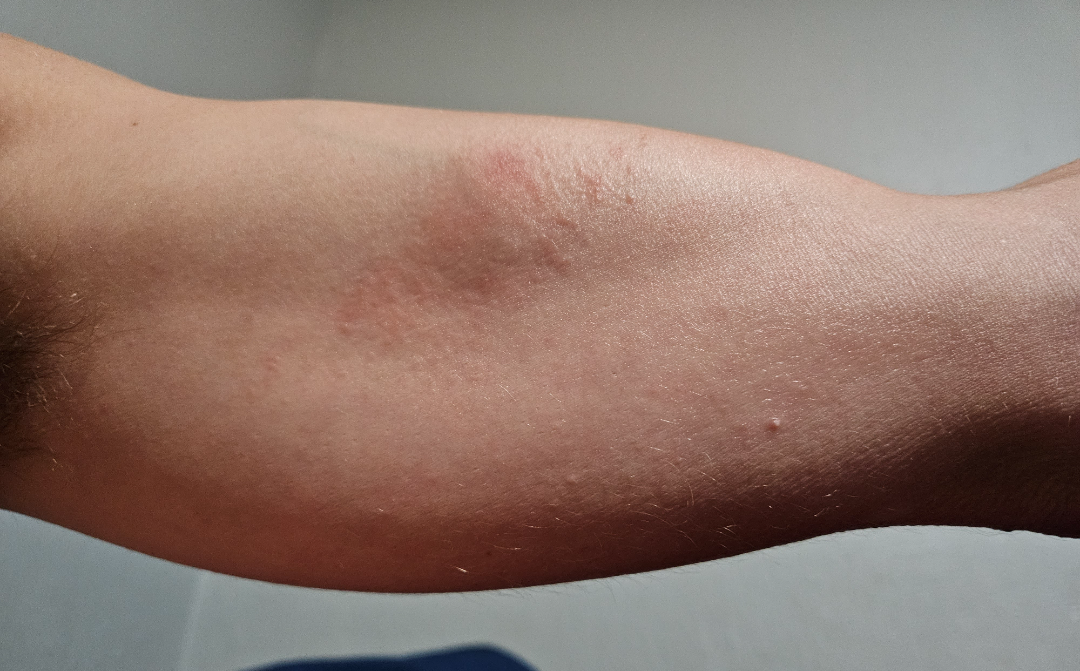| feature | finding |
|---|---|
| diagnostic considerations | the leading impression is Allergic Contact Dermatitis; the differential also includes Eczema |